A dermoscopic photograph of a skin lesion:
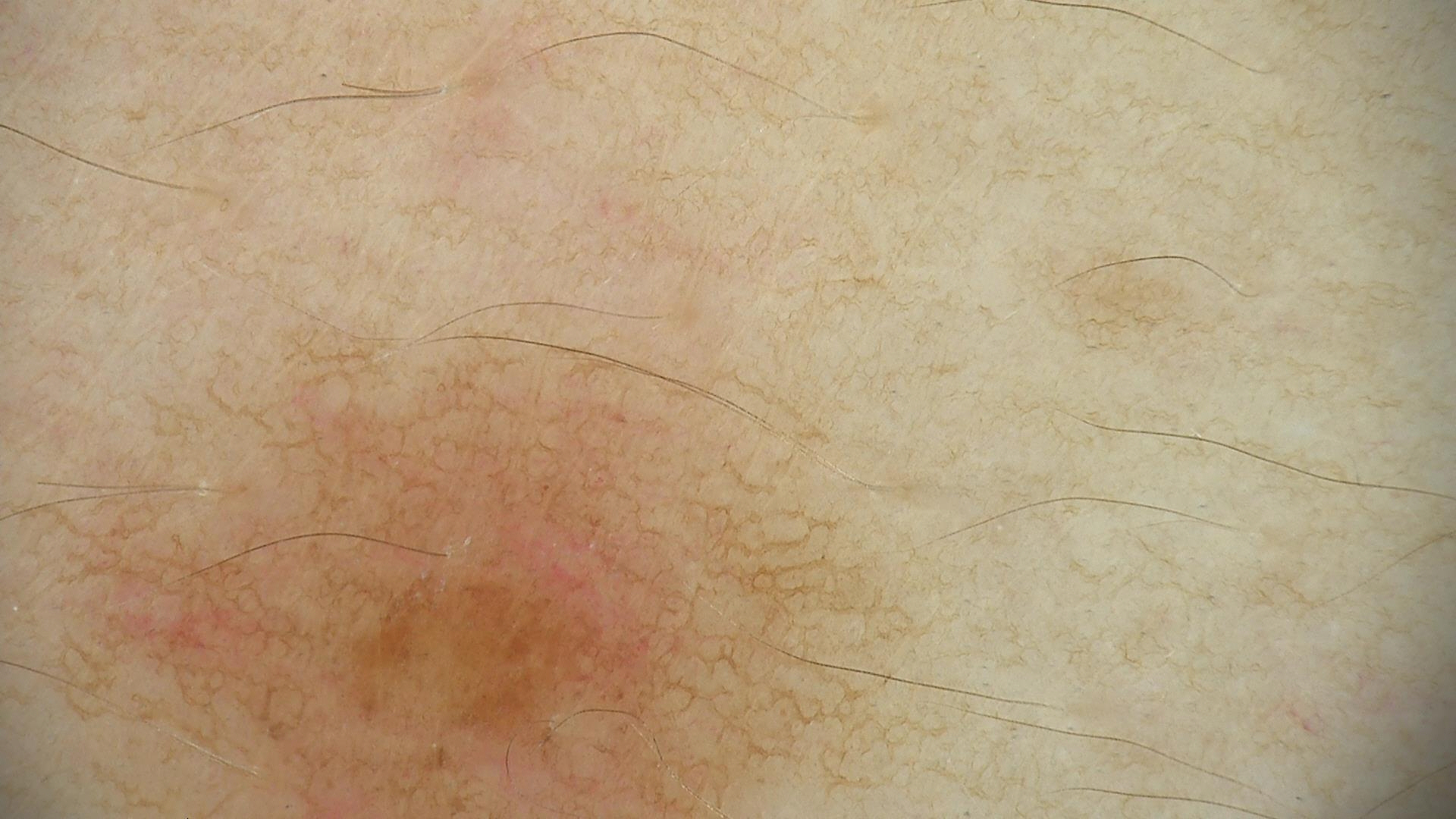| key | value |
|---|---|
| diagnosis | dysplastic junctional nevus (expert consensus) |